Fitzpatrick skin type II · a female patient aged 63-67 · per the chart, a prior melanoma: 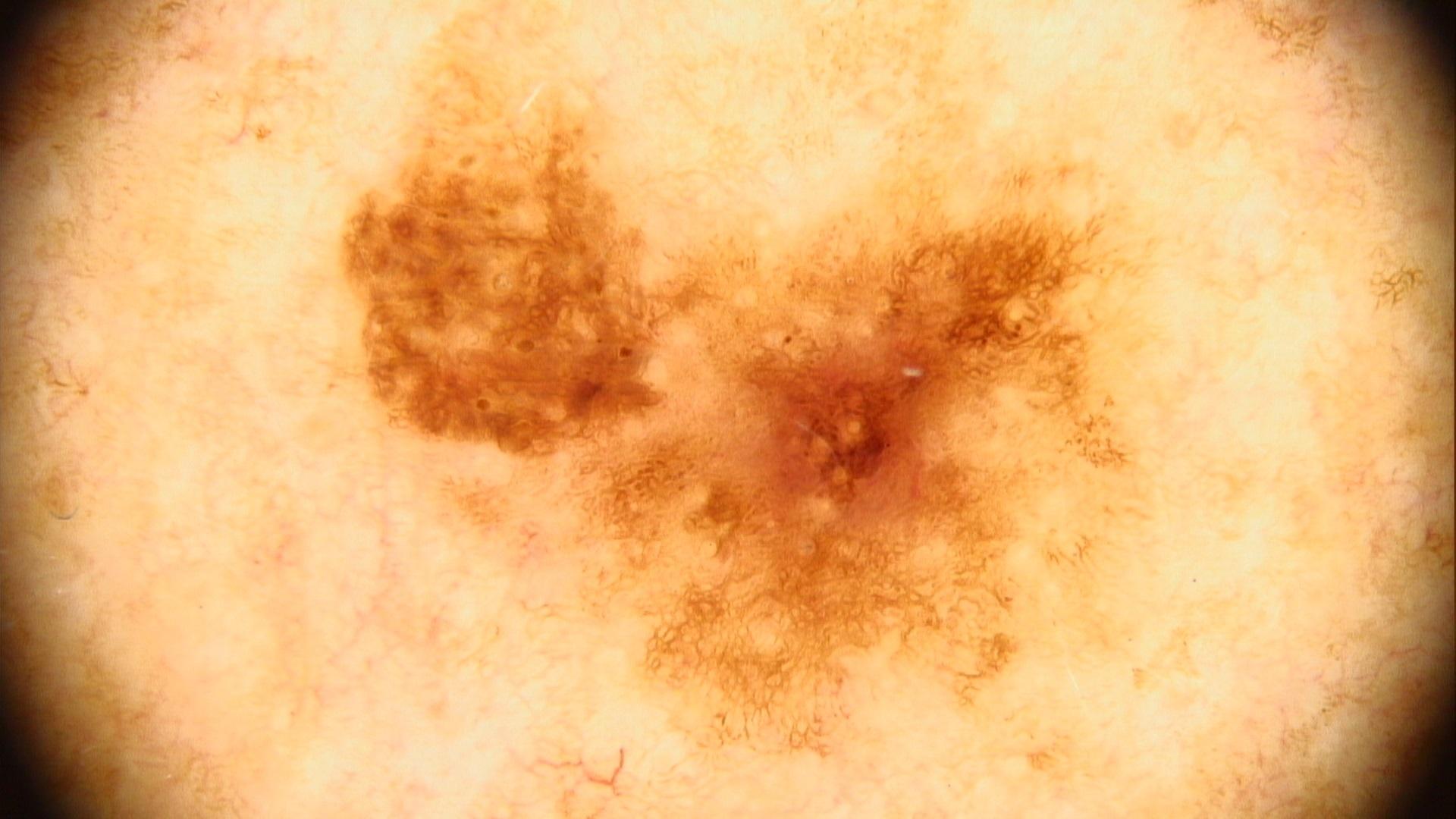<case>
<diagnosis>
<name>Nevus</name>
<malignancy>benign</malignancy>
<confirmation>histopathology</confirmation>
<lineage>melanocytic</lineage>
</diagnosis>
</case>